Located on the back of the hand · the photograph is a close-up of the affected area · the contributor is 40–49, female: 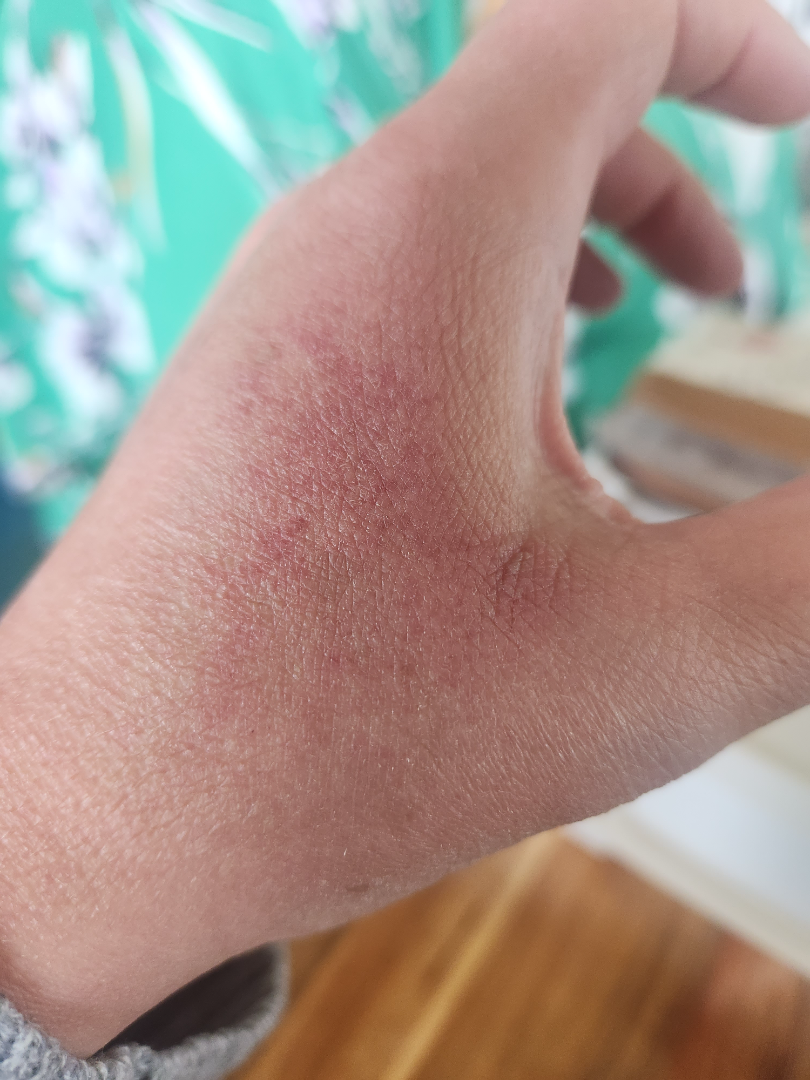Most consistent with Eczema; also consider Irritant Contact Dermatitis; a more distant consideration is Allergic Contact Dermatitis.